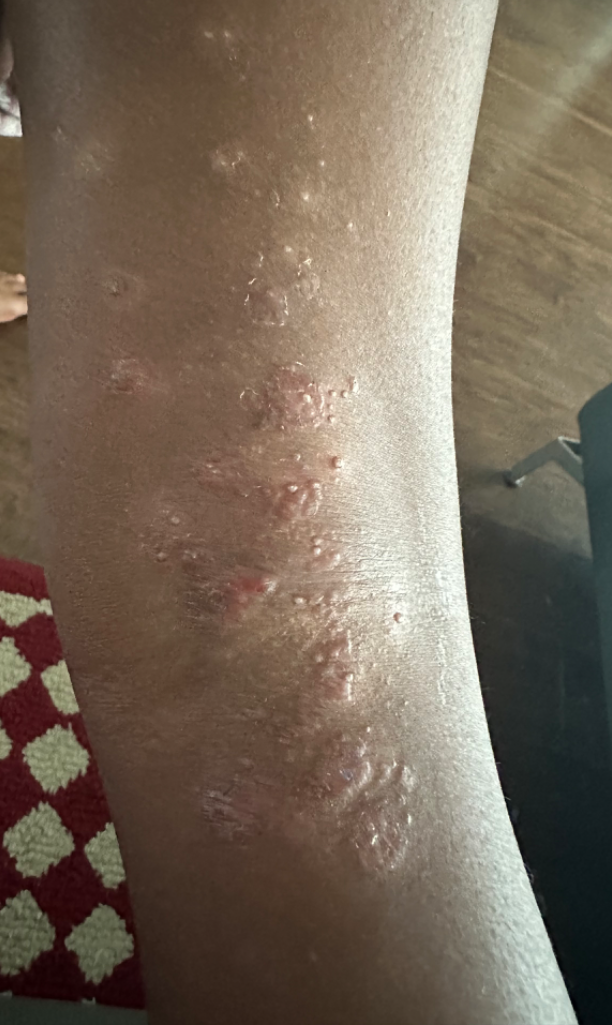The case was indeterminate on photographic review.
The leg is involved.
Texture is reported as fluid-filled and raised or bumpy.
The condition has been present for three to twelve months.
Reported lesion symptoms include burning, bothersome appearance, enlargement and itching.
The patient considered this a rash.
The photo was captured at an angle.
No associated systemic symptoms reported.